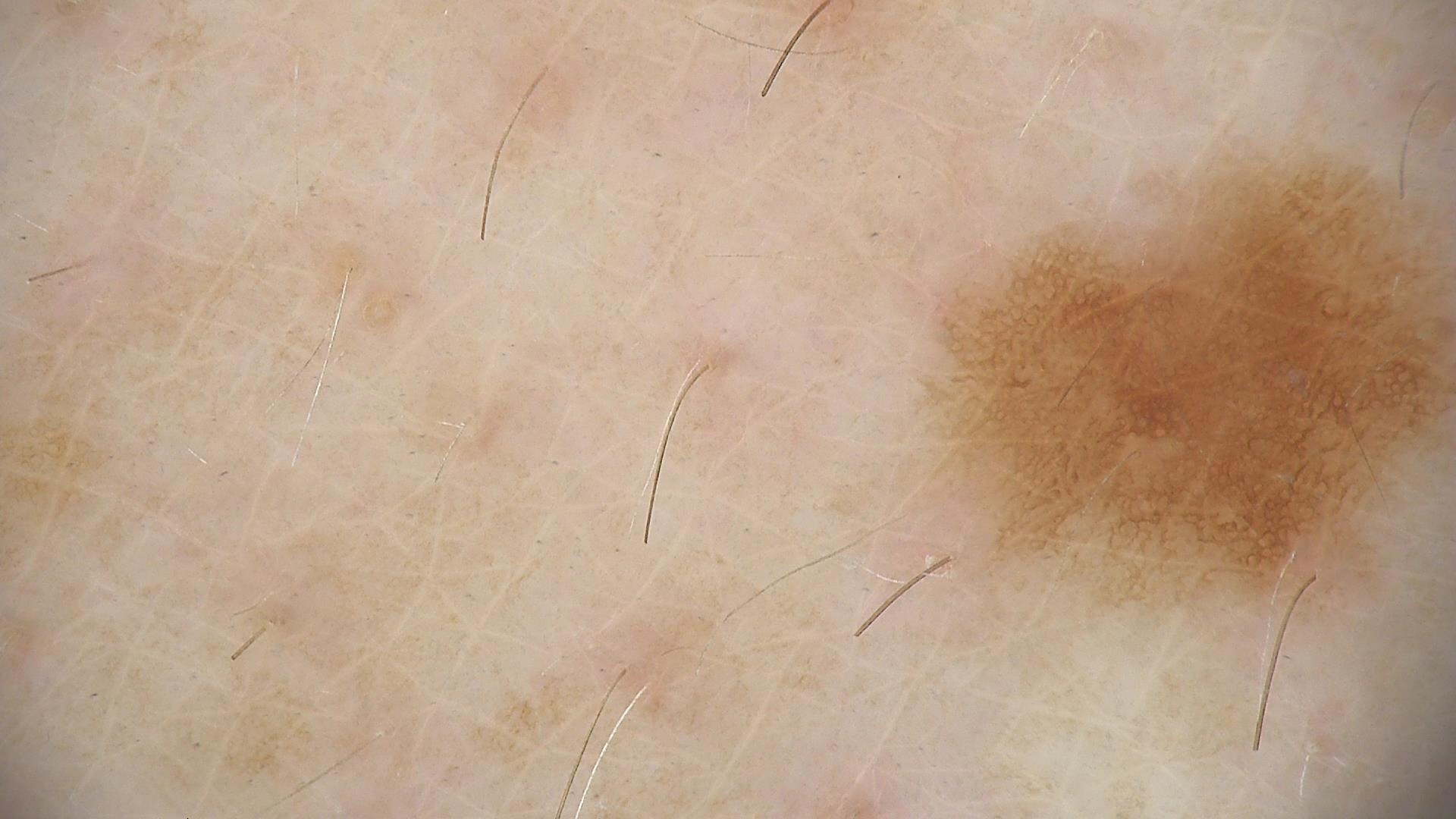Classified as a dysplastic junctional nevus.